No relevant systemic symptoms; skin tone: non-clinician graders estimated a MST of 2; this image was taken at a distance; the affected area is the sole of the foot; present for one to four weeks; the lesion is described as fluid-filled and flat: 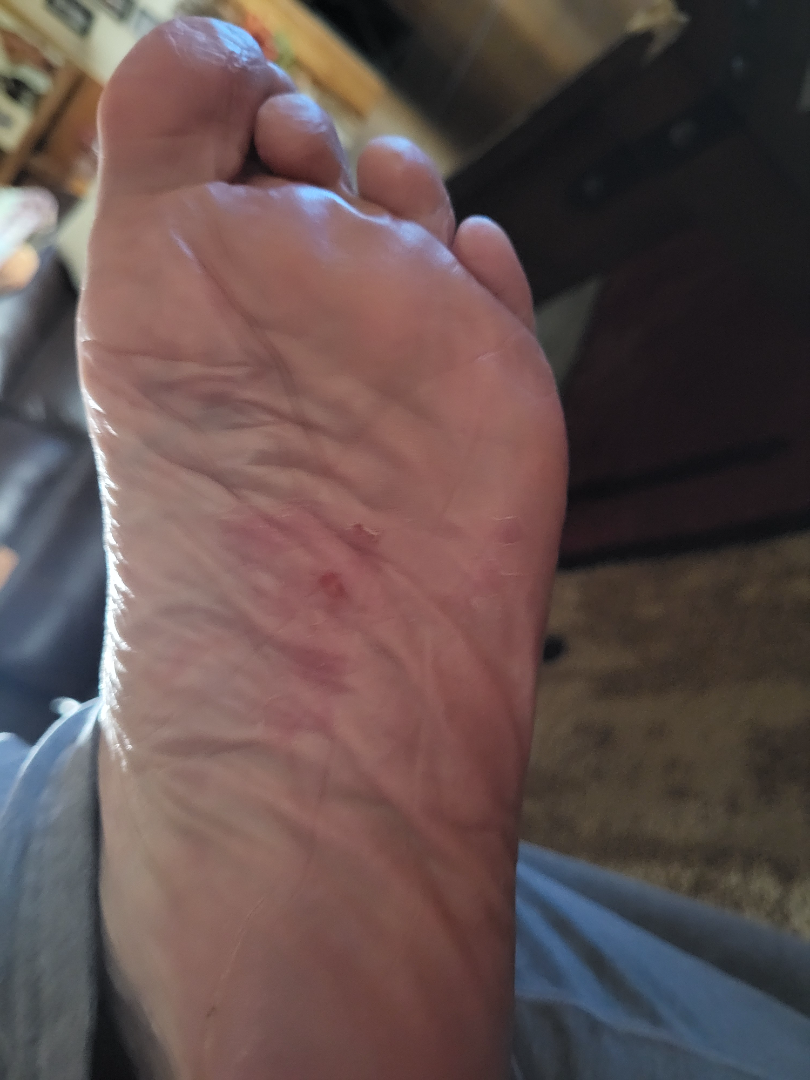Tinea (1.00).